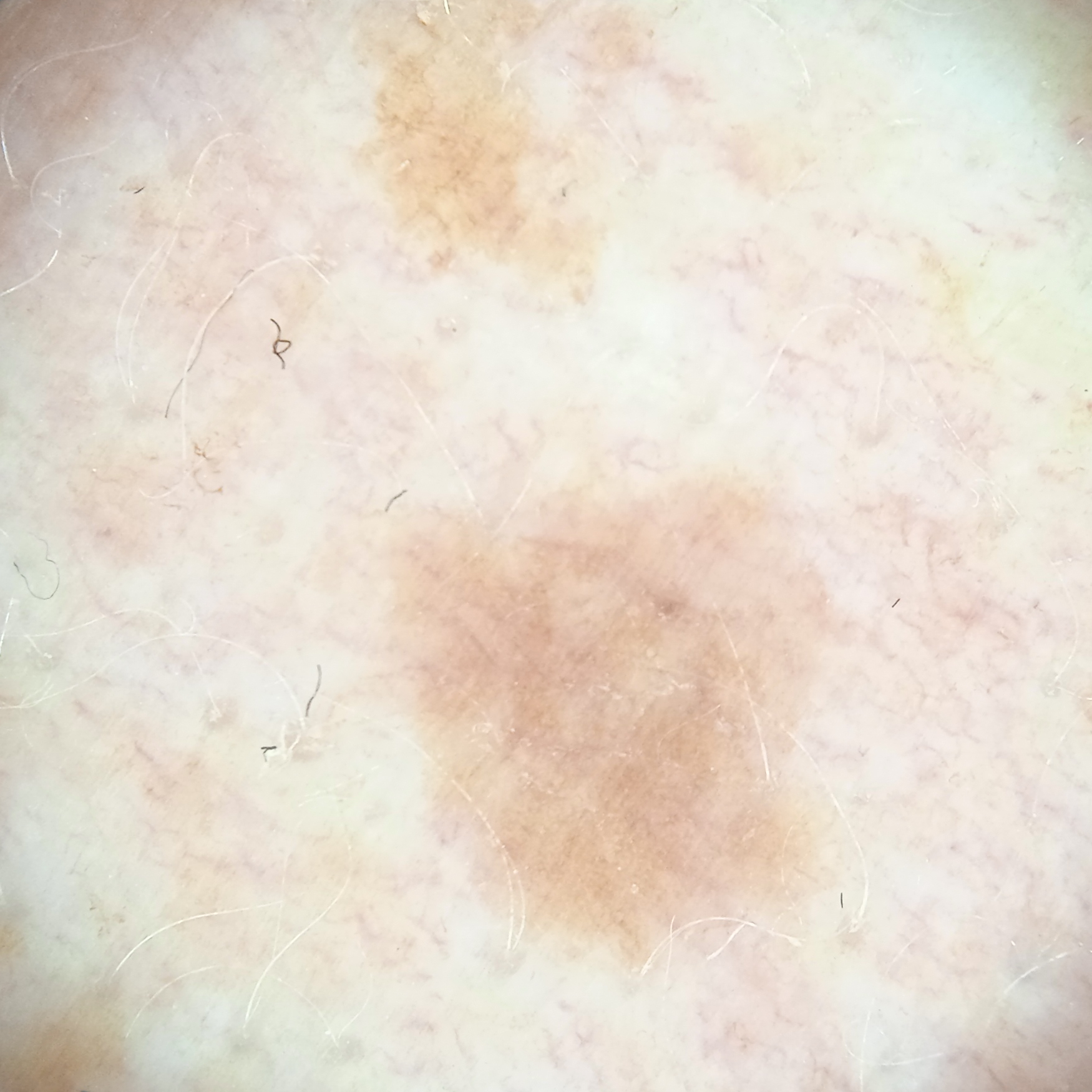{
  "mole_burden": "a moderate number of melanocytic nevi",
  "referral": "research study (no referral diagnosis)",
  "lesion_location": "an arm",
  "diagnosis": {
    "name": "melanocytic nevus",
    "malignancy": "benign"
  }
}